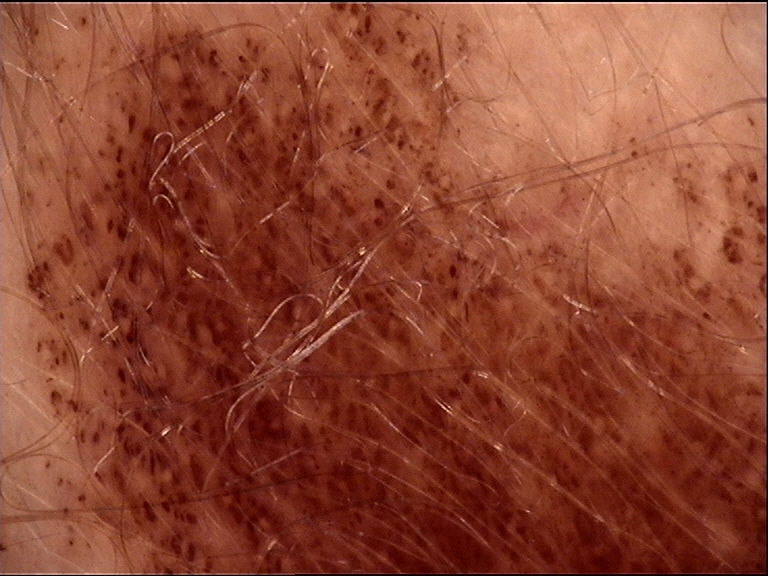diagnosis:
  name: congenital junctional nevus
  code: cjb
  malignancy: benign
  super_class: melanocytic
  confirmation: expert consensus